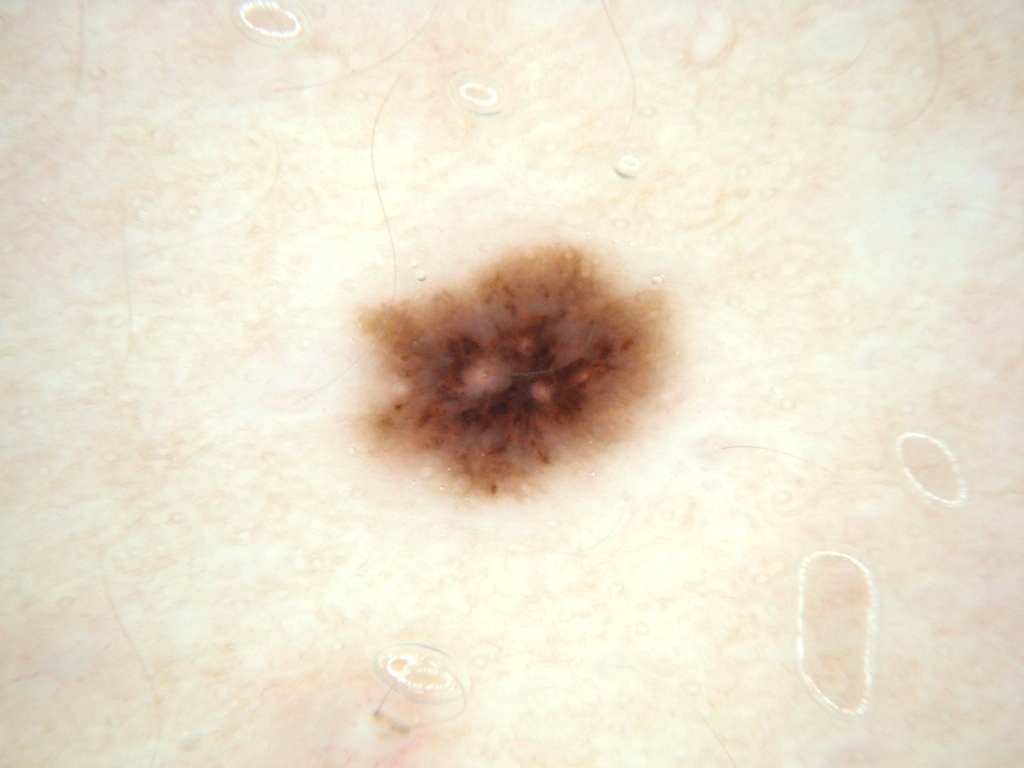{"image": {"modality": "dermoscopy"}, "patient": {"sex": "male", "age_approx": 15}, "dermoscopic_features": {"present": ["milia-like cysts"], "absent": ["streaks", "globules", "pigment network", "negative network"]}, "lesion_location": {"bbox_xyxy": [353, 241, 674, 500]}, "diagnosis": {"name": "melanocytic nevus", "malignancy": "benign", "lineage": "melanocytic", "provenance": "clinical"}}